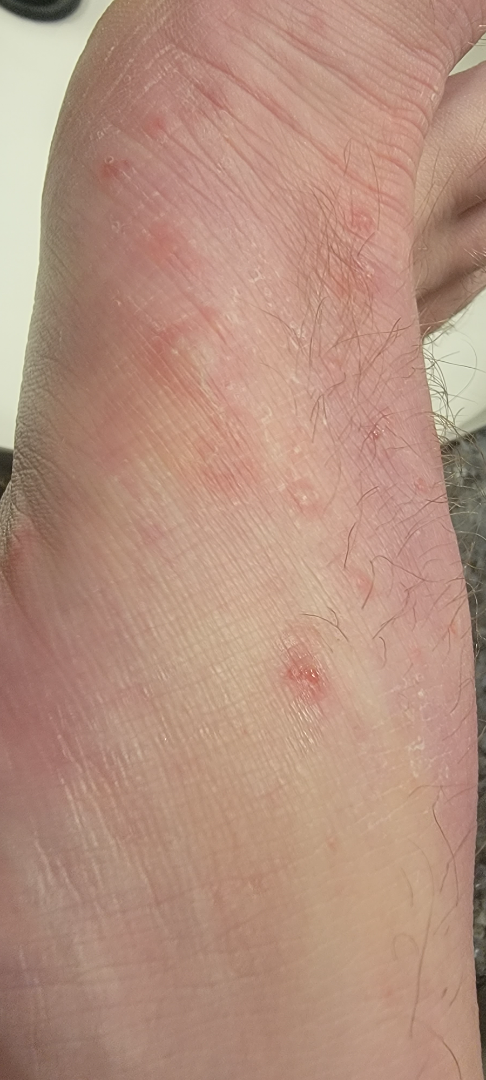The arm, back of the hand, palm and top or side of the foot are involved. The contributor is a male aged 30–39. This image was taken at an angle. On remote review of the image: Psoriasis (considered); Insect Bite (considered); Folliculitis (lower probability); Dermatitis herpetiformis (lower probability); Acute dermatitis, NOS (lower probability); Skin and soft tissue atypical mycobacterial infection (lower probability); Perforating dermatosis (lower probability).